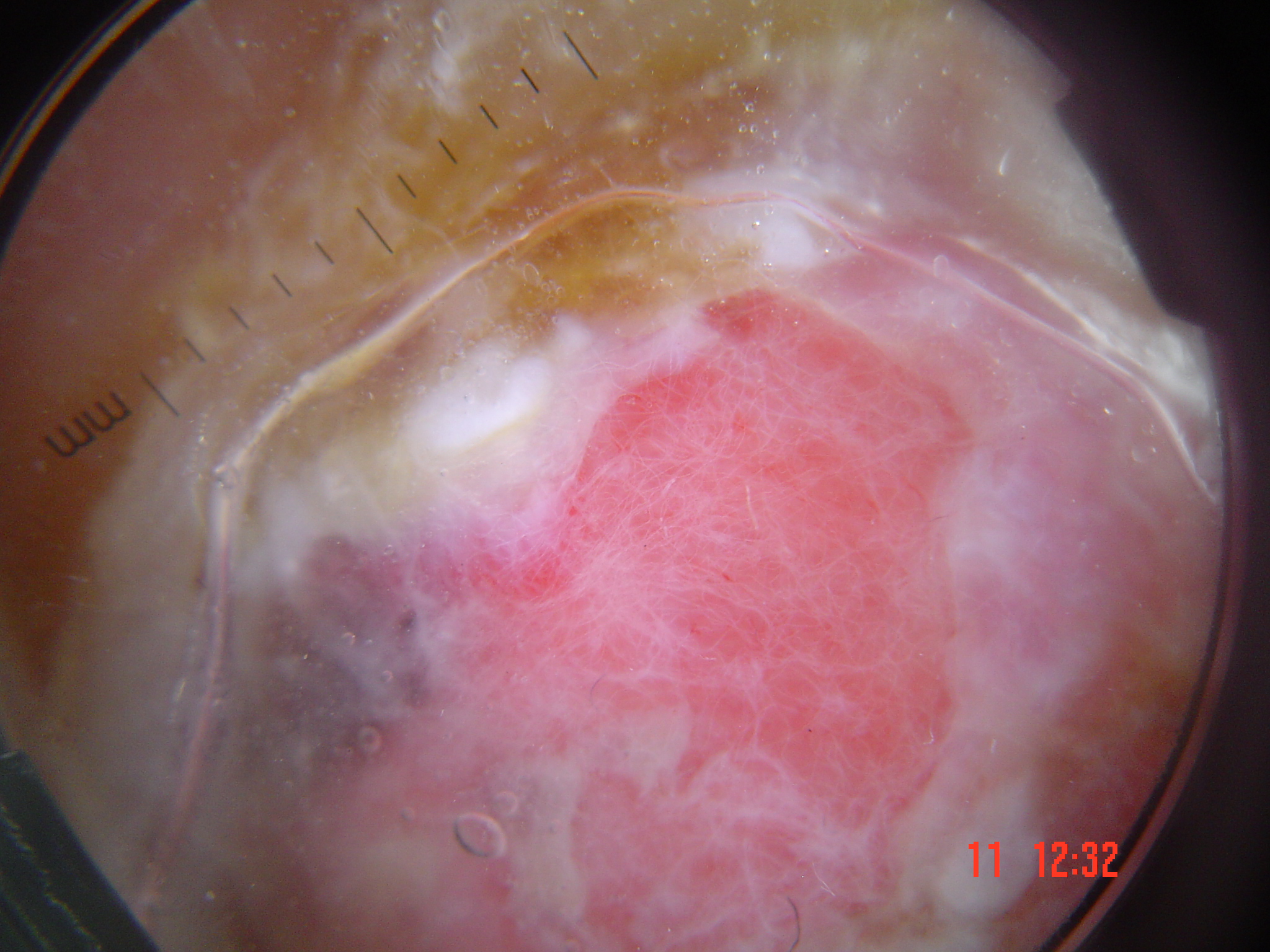class — acral nodular melanoma (biopsy-proven)